The photograph was taken at a distance, the lesion involves the leg: 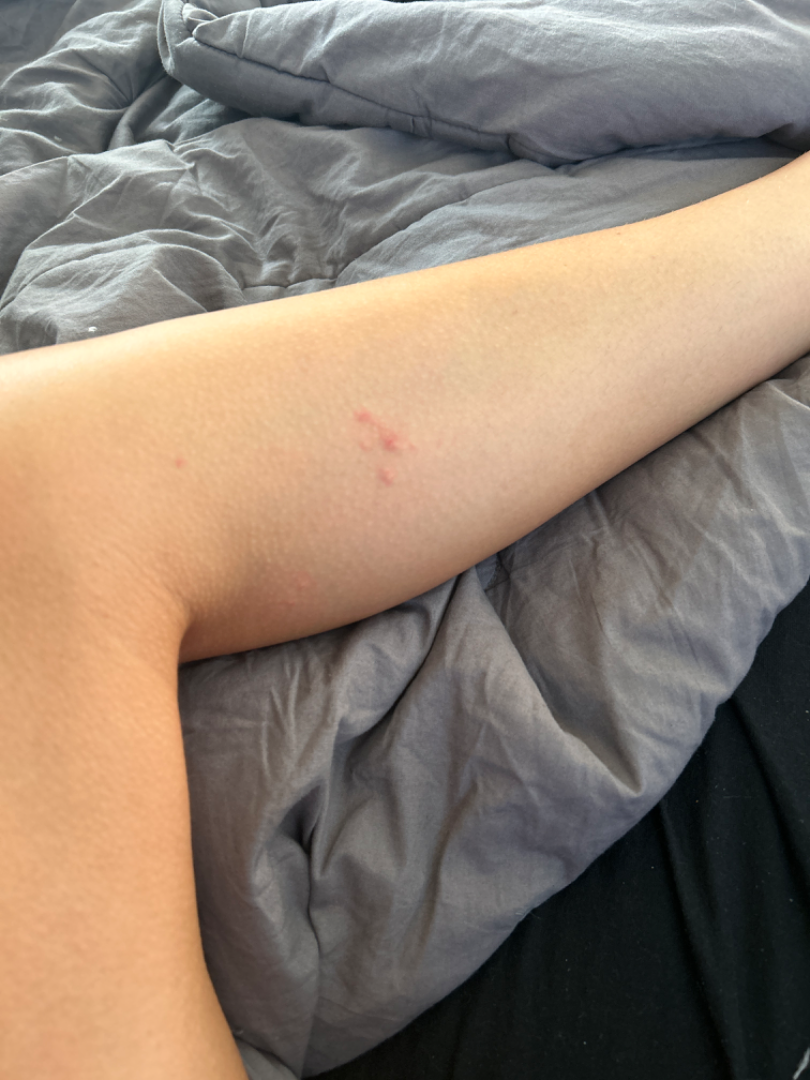Case summary:
- patient describes the issue as · a rash
- constitutional symptoms · none reported
- described texture · raised or bumpy
- patient-reported symptoms · itching
- differential diagnosis · Insect Bite, Allergic Contact Dermatitis and Herpes Simplex were considered with similar weight